A male patient aged approximately 70 · a dermoscopic close-up of a skin lesion.
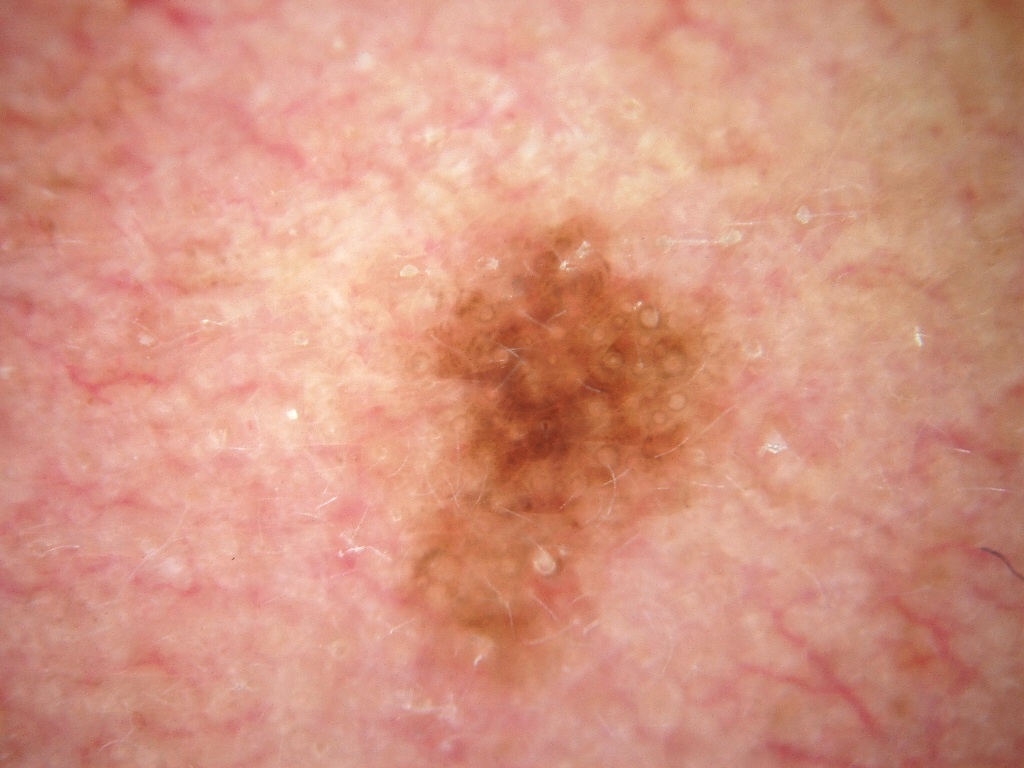In (x1, y1, x2, y2) order, the lesion's extent is bbox(396, 214, 735, 702).
The dermoscopic pattern shows no milia-like cysts, globules, streaks, pigment network, or negative network.
The lesion covers approximately 13% of the dermoscopic field.
Histopathology confirmed a melanoma, a malignancy.